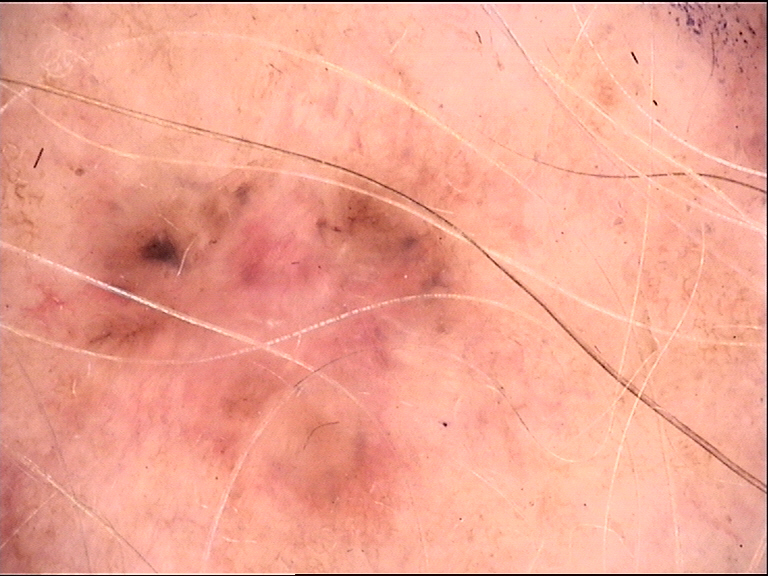Dermoscopy of a skin lesion. The morphology is that of a keratinocytic lesion. Histopathologically confirmed as a malignancy — a basal cell carcinoma.